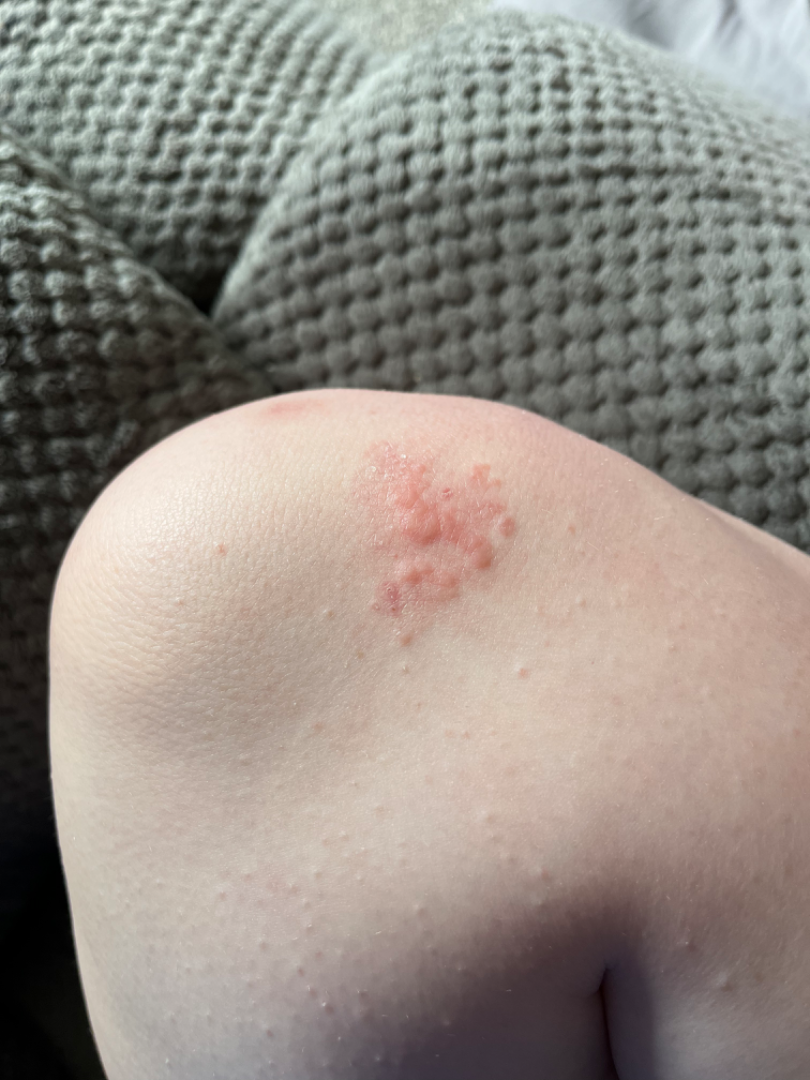On remote review of the image, Acute dermatitis, NOS (most likely).